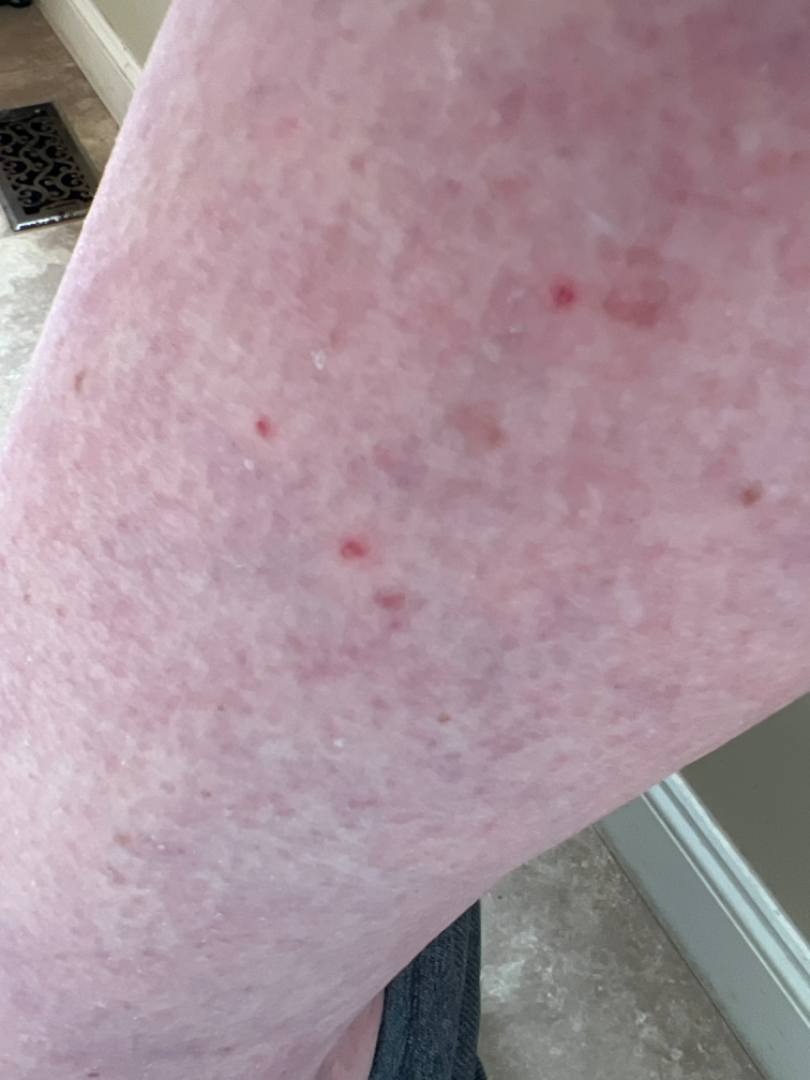Q: What was the assessment?
A: not assessable
Q: What is the framing?
A: close-up
Q: Any systemic symptoms?
A: joint pain, fatigue and fever
Q: What is the lesion texture?
A: raised or bumpy
Q: Reported symptoms?
A: pain
Q: Where on the body?
A: leg
Q: How long has this been present?
A: one to four weeks
Q: Patient demographics?
A: female, age 40–49